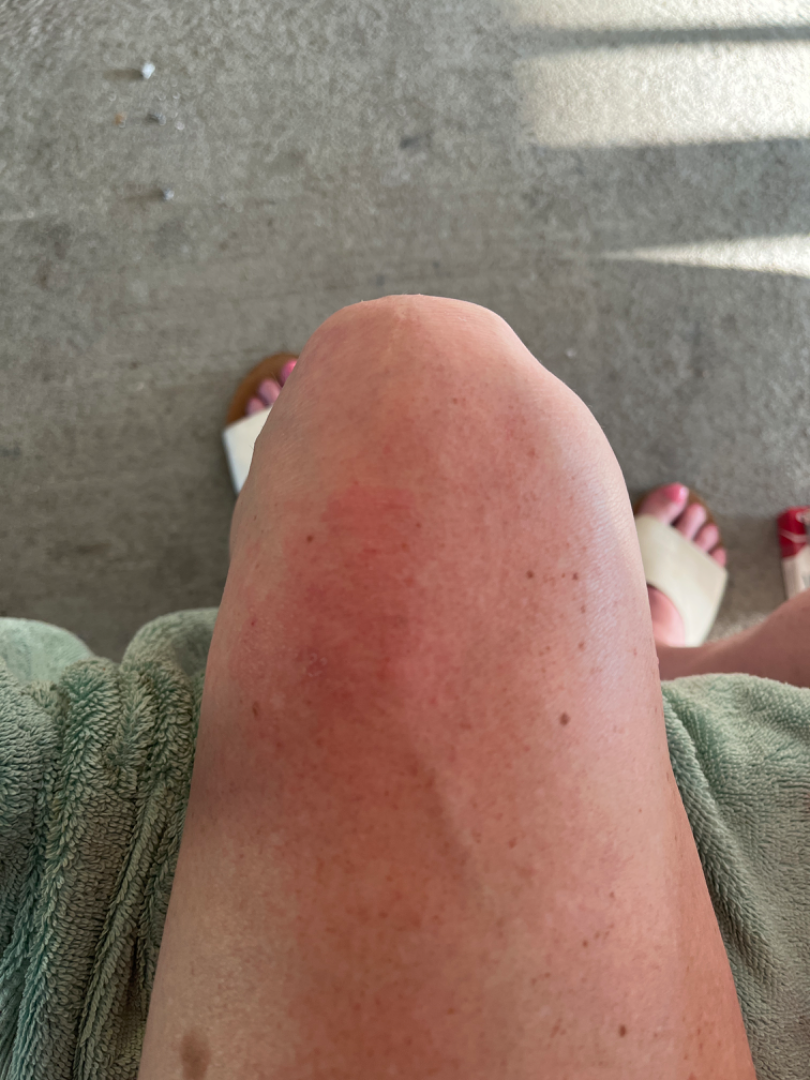Self-categorized by the patient as a rash. Skin tone: Fitzpatrick phototype II; human graders estimated Monk skin tone scale 3 (US pool) or 2 (India pool). Reported lesion symptoms include itching. The condition has been present for one to three months. The photo was captured at a distance. The lesion is described as raised or bumpy. The lesion involves the leg. The subject is 50–59, female. On remote review of the image, the leading consideration is Eczema; also raised was Allergic Contact Dermatitis; possibly Abrasion, scrape, or scab; lower on the differential is Psoriasis.